A patient 50 years of age. A clinical photo of a skin lesion taken with a smartphone:
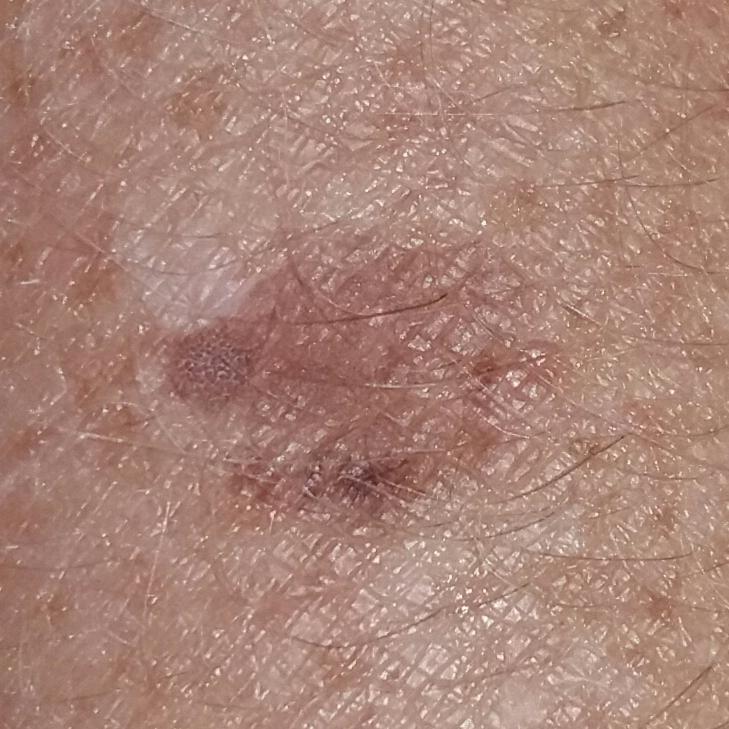Clinical context: The patient reports no symptoms. Impression: Expert review favored a seborrheic keratosis.